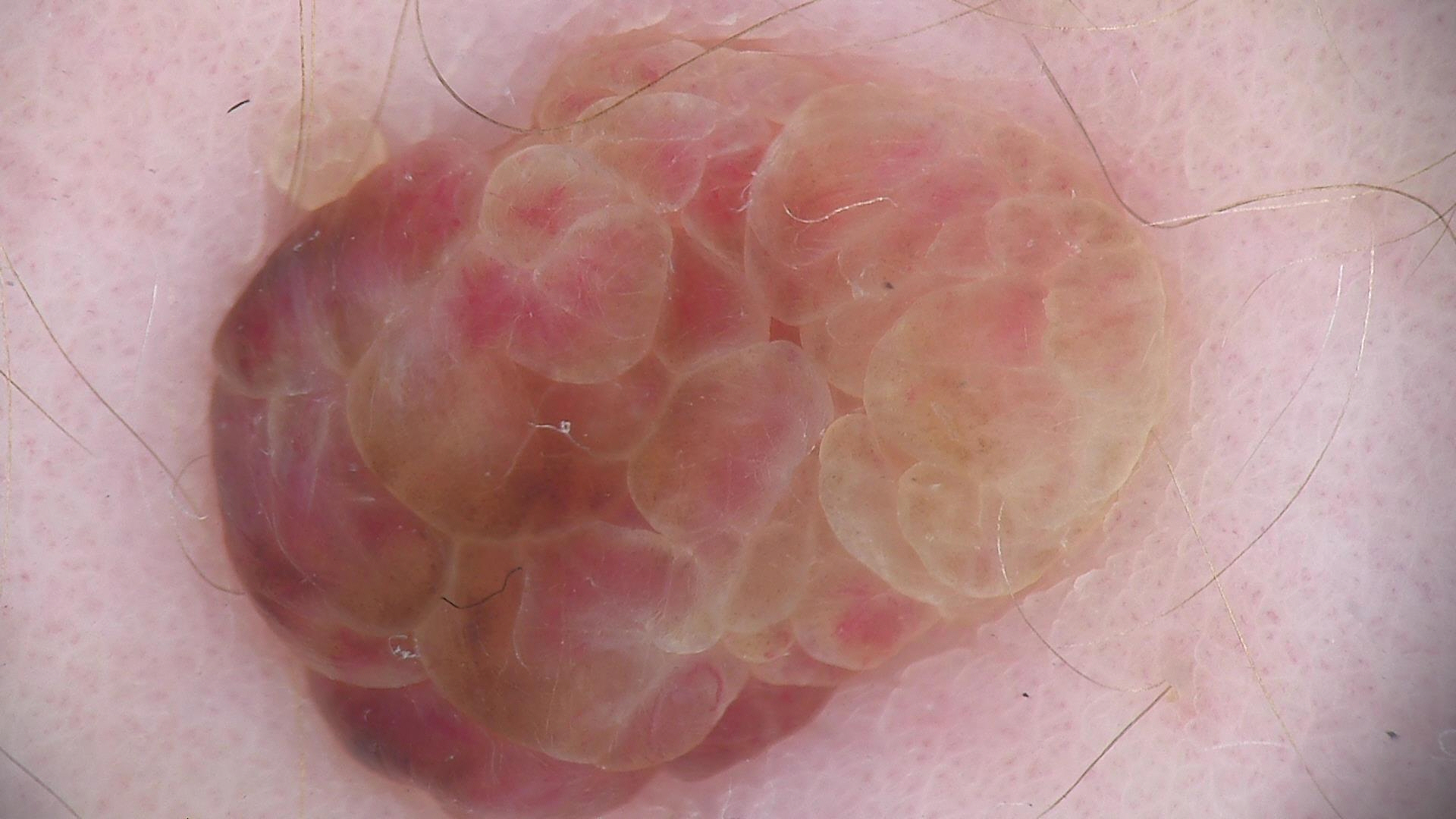Conclusion:
Classified as a dermal nevus.